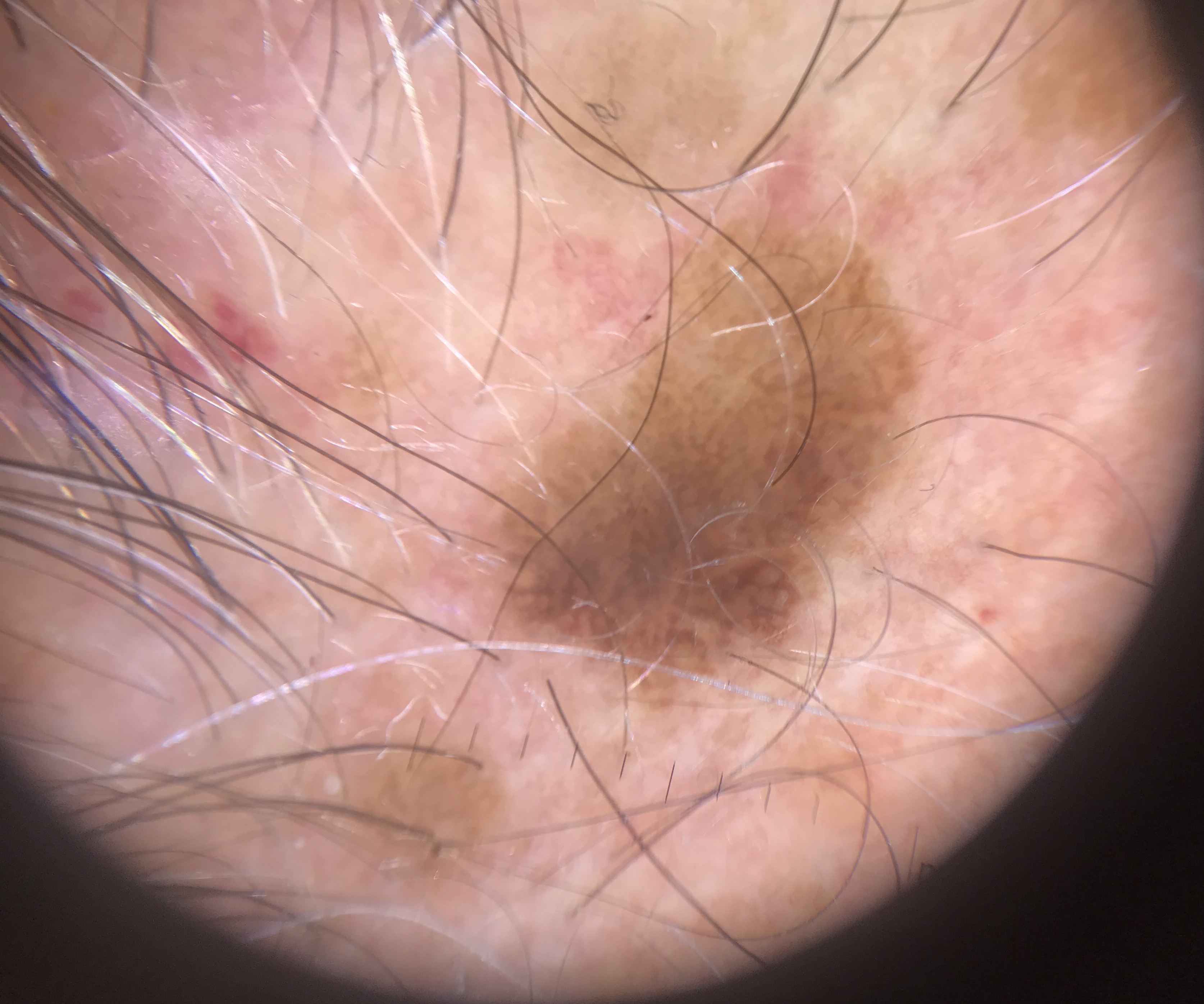A dermoscopic photograph of a skin lesion.
Diagnosed as a keratinocytic, benign lesion — a seborrheic keratosis.